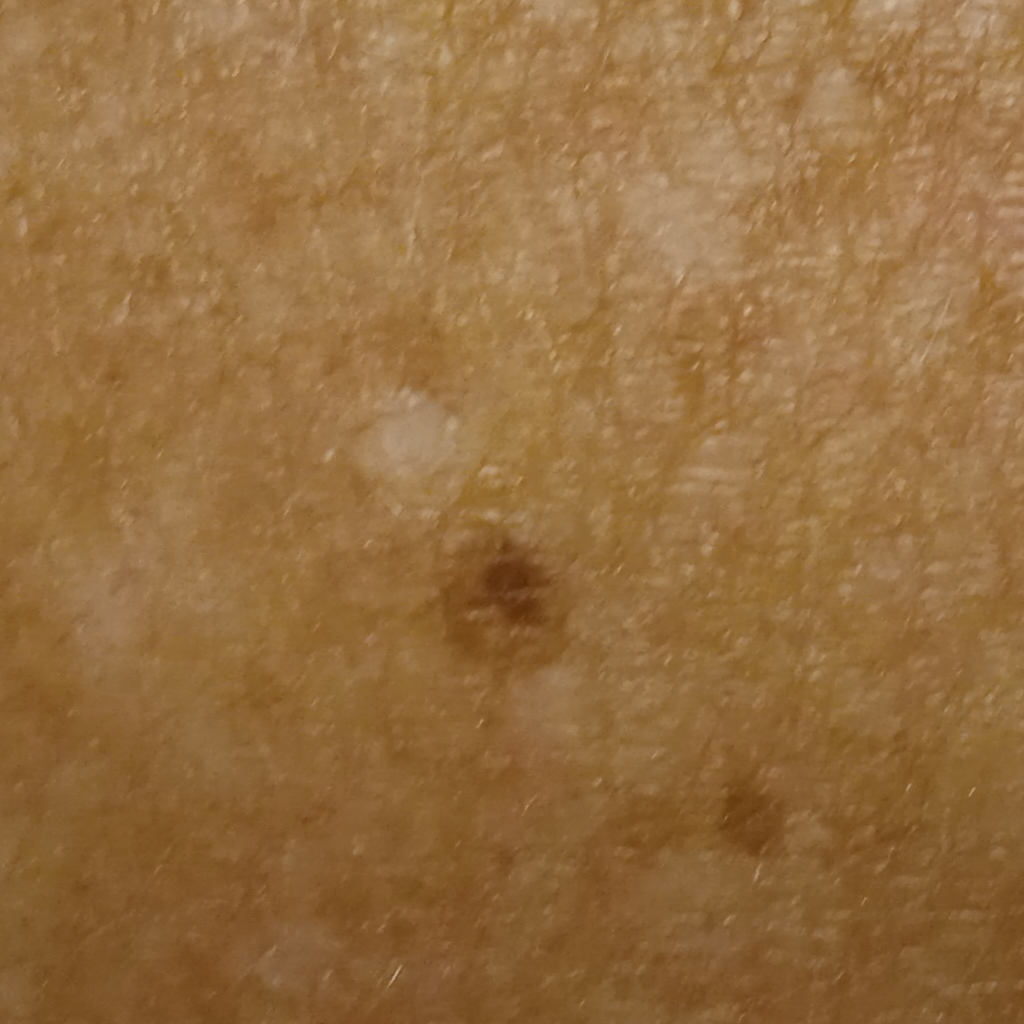A female patient aged 75. The patient describes having a moderate number of moles. On a questionnaire the patient reported a personal history of cancer and a personal history of skin cancer. Imaged for a research study, with no referral diagnosis recorded. Located on the back. The lesion is about 2.7 mm across. The dermatologists' assessment was a melanocytic nevus.